The photograph is a close-up of the affected area. The contributor is 18–29, female. The top or side of the foot is involved:
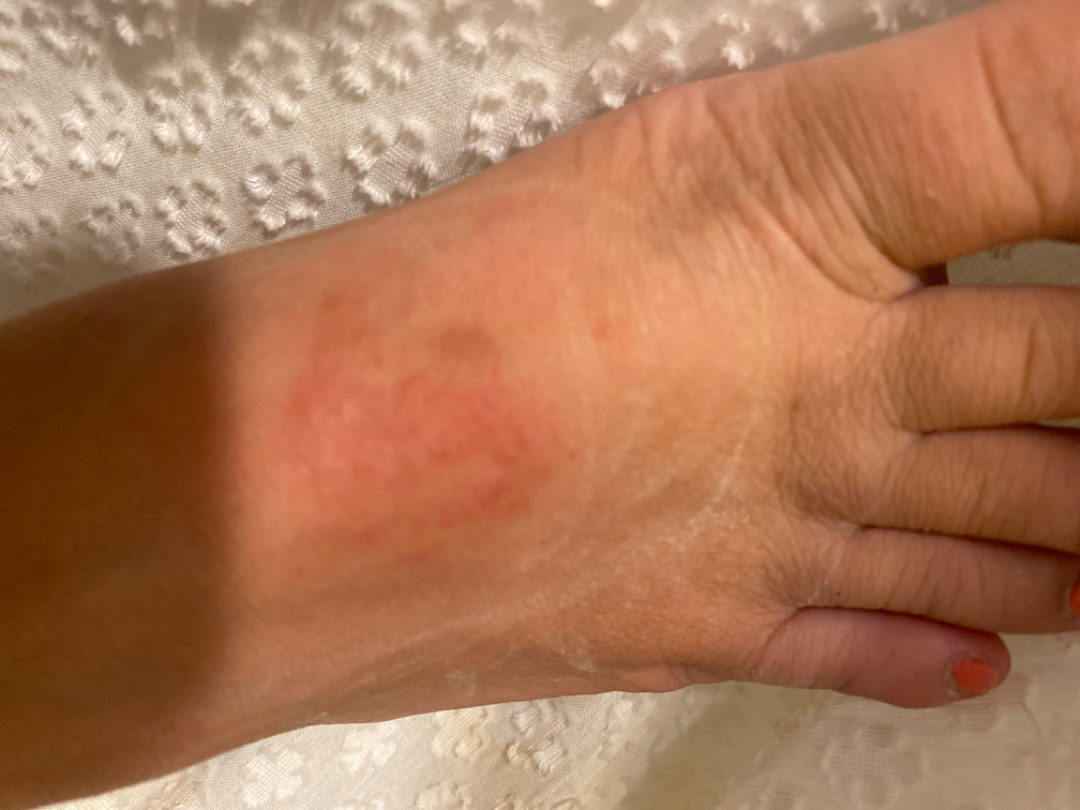On dermatologist assessment of the image: favoring Allergic Contact Dermatitis; possibly Acute and chronic dermatitis.